Dermoscopy of a skin lesion.
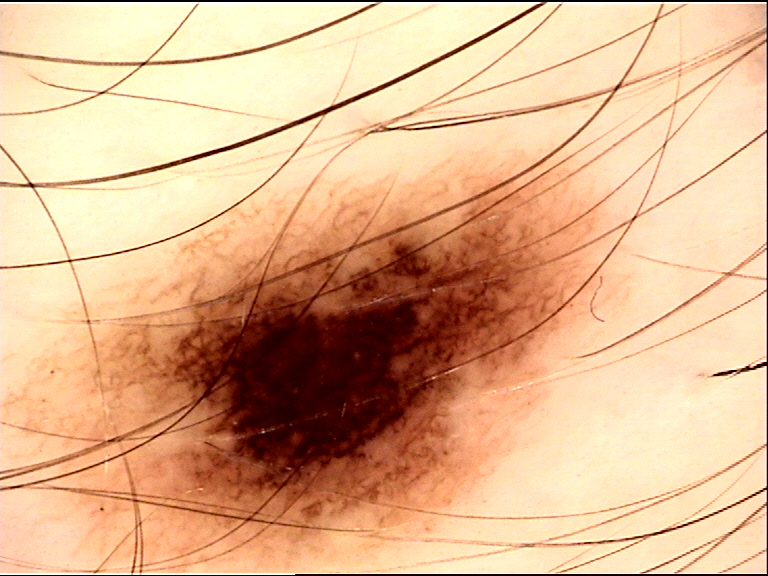<case>
<diagnosis>
<name>dysplastic compound nevus</name>
<code>cd</code>
<malignancy>benign</malignancy>
<super_class>melanocytic</super_class>
<confirmation>expert consensus</confirmation>
</diagnosis>
</case>